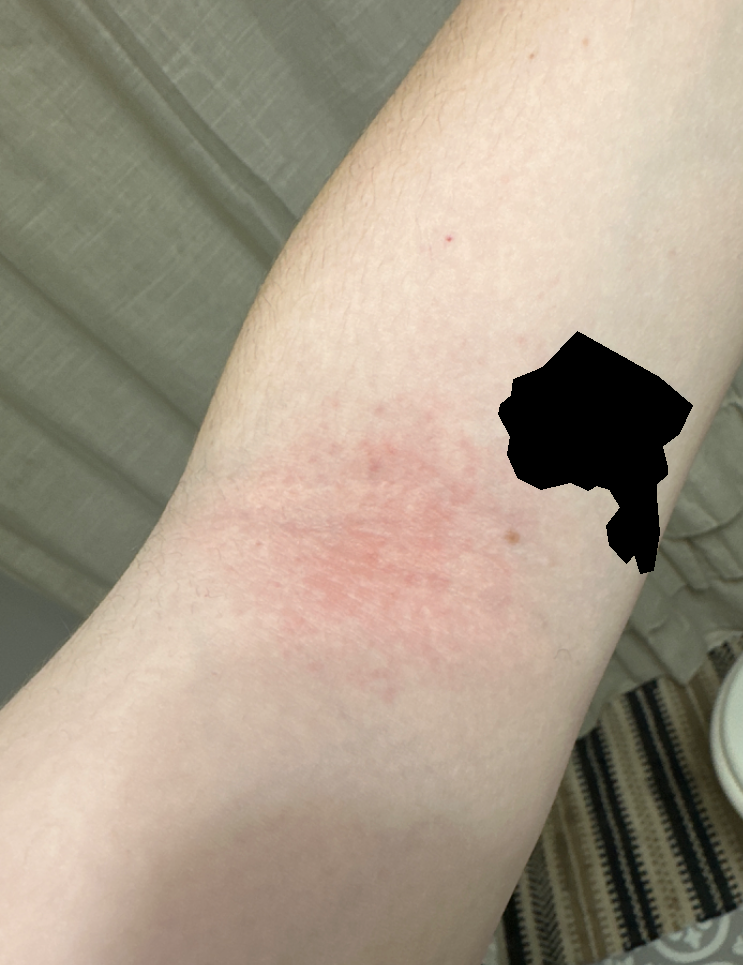shot type: close-up
patient describes the issue as: a rash
constitutional symptoms: none reported
site: arm
onset: about one day
texture: raised or bumpy
clinical impression: consistent with Eczema